This is a close-up image · reported duration is about one day · the patient notes the lesion is flat · self-categorized by the patient as a rash · the patient is 18–29, female · the lesion involves the leg · no constitutional symptoms were reported: 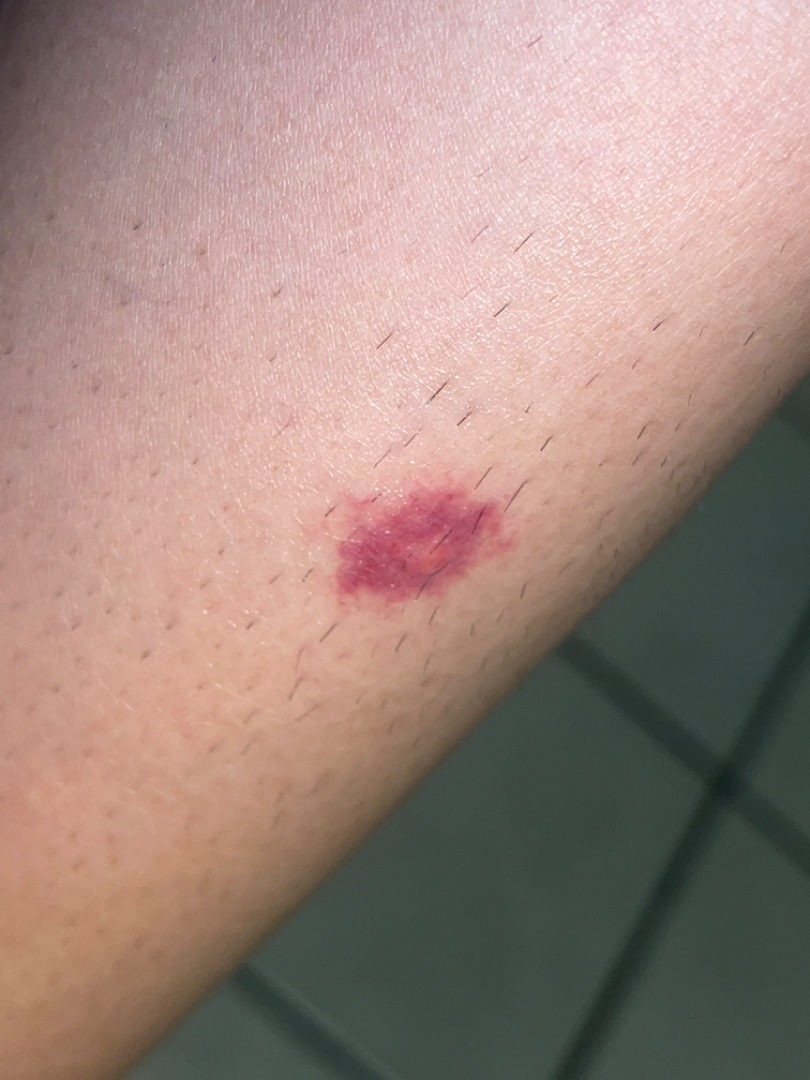<dermatology_case>
  <differential>
    <leading>Purpura</leading>
    <considered>Insect Bite</considered>
    <unlikely>Benign cutaneous vascular tumor, Pigmented purpuric eruption</unlikely>
  </differential>
</dermatology_case>